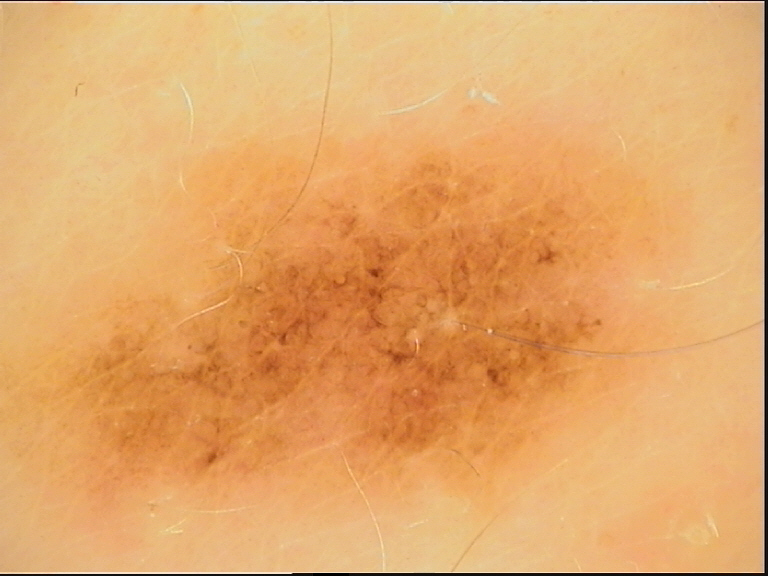image: dermoscopy
diagnosis:
  name: dysplastic junctional nevus
  code: jd
  malignancy: benign
  super_class: melanocytic
  confirmation: expert consensus